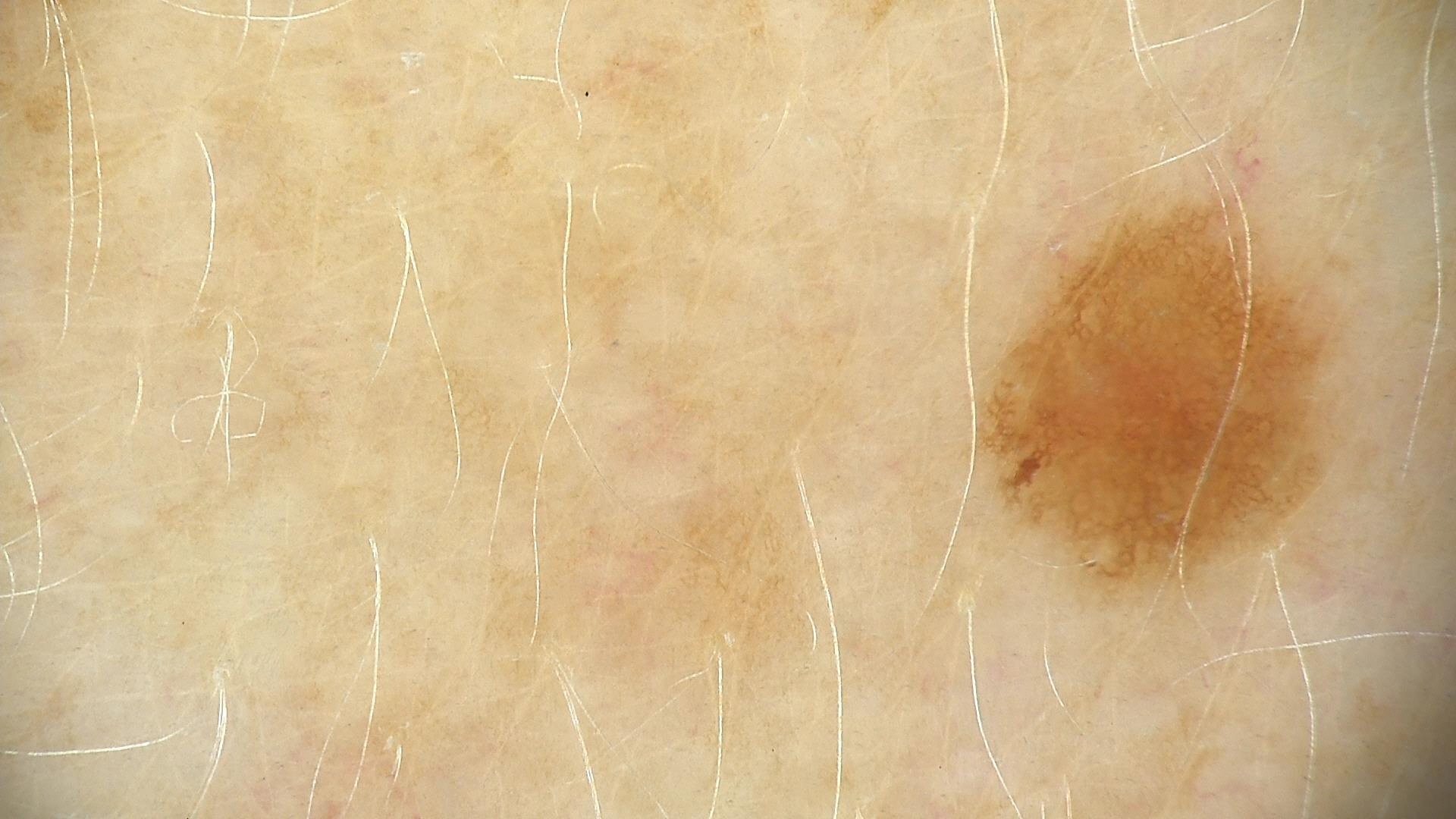A dermatoscopic image of a skin lesion.
Consistent with a dysplastic junctional nevus.